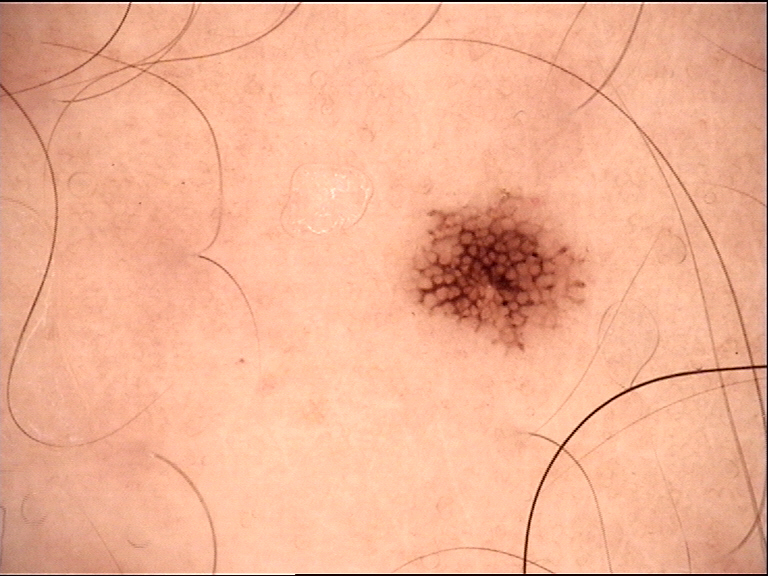Case:
A dermoscopic image of a skin lesion.
Impression:
The diagnostic label was a benign lesion — a dysplastic junctional nevus.